Skin tone: FST II; lay reviewers estimated Monk Skin Tone 2 · the photograph is a close-up of the affected area · texture is reported as raised or bumpy · located on the arm · the contributor is 18–29, male · the condition has been present for less than one week · self-categorized by the patient as a rash · the lesion is associated with itching — 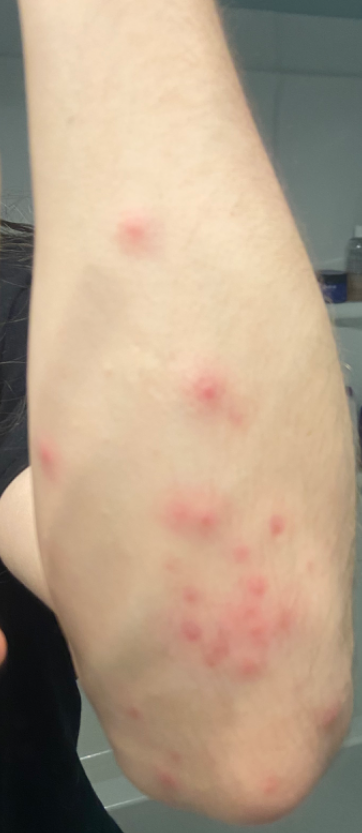Three dermatologists independently reviewed the case: the leading consideration is Insect Bite; also consider Folliculitis; less probable is Granuloma annulare.